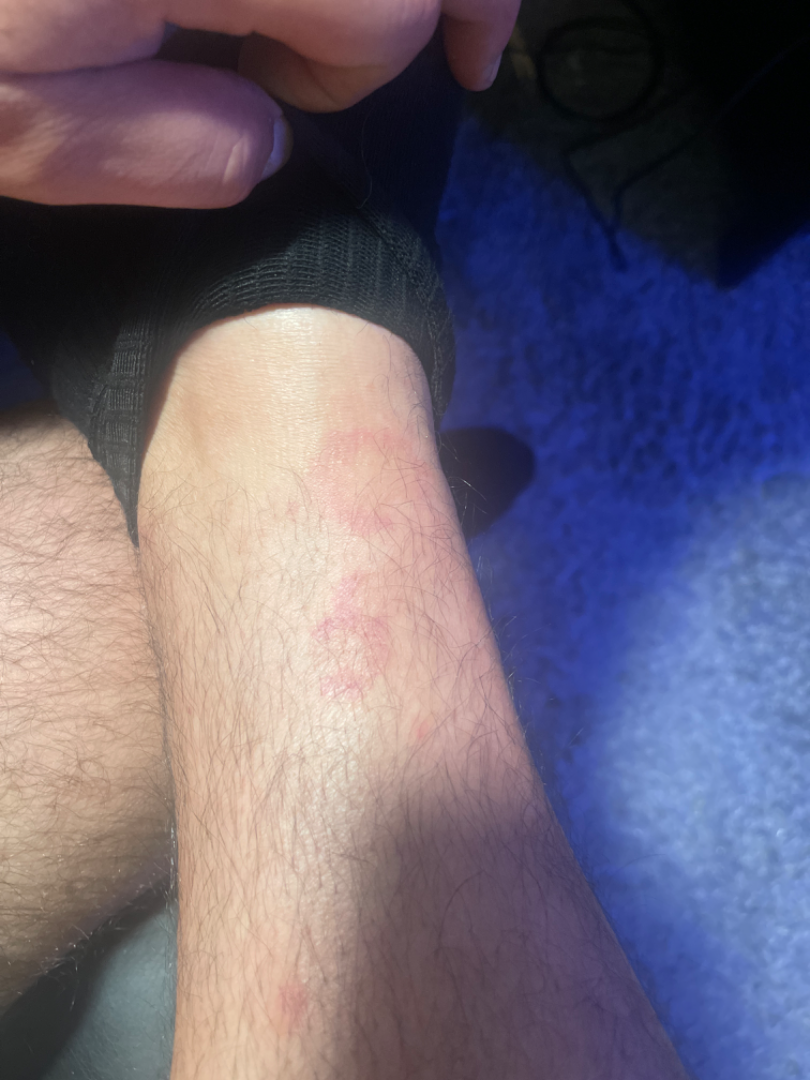Review: The dermatologist could not determine a likely condition from the photograph alone. Patient information: The leg is involved. The patient did not report lesion symptoms. Close-up view. The patient is male. Present for about one day. Self-categorized by the patient as a rash. The contributor reports the lesion is flat. Skin tone: FST IV; lay graders estimated a Monk skin tone scale of 2.